The patient reported no systemic symptoms, this image was taken at an angle, the condition has been present for one to four weeks, the lesion is described as raised or bumpy, the subject is a female aged 40–49, the lesion involves the top or side of the foot: 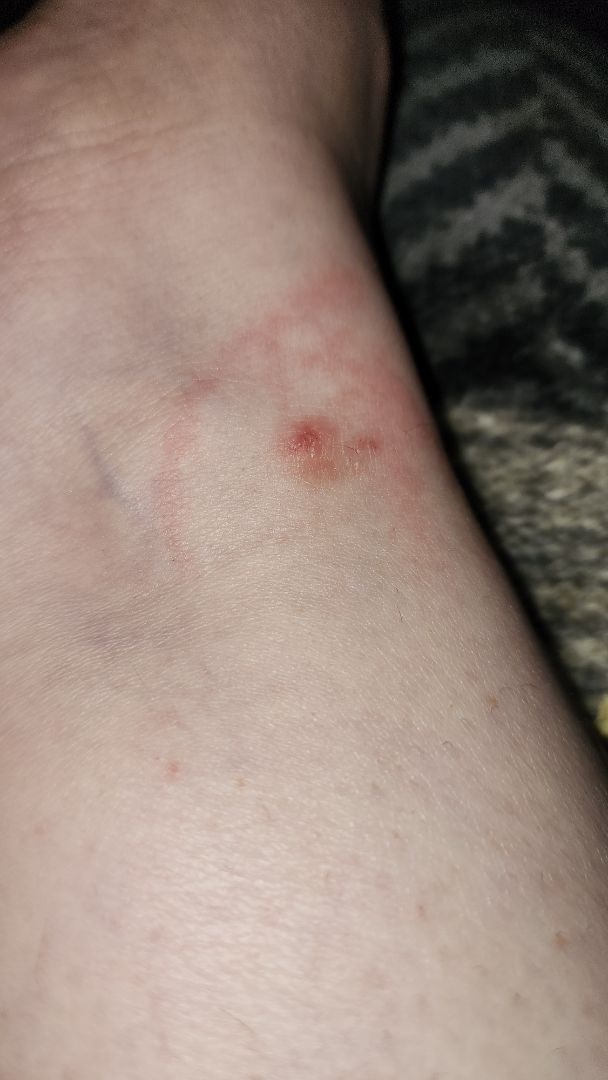One reviewing dermatologist: most consistent with Insect Bite; also consider Allergic Contact Dermatitis; less likely is Urticaria.